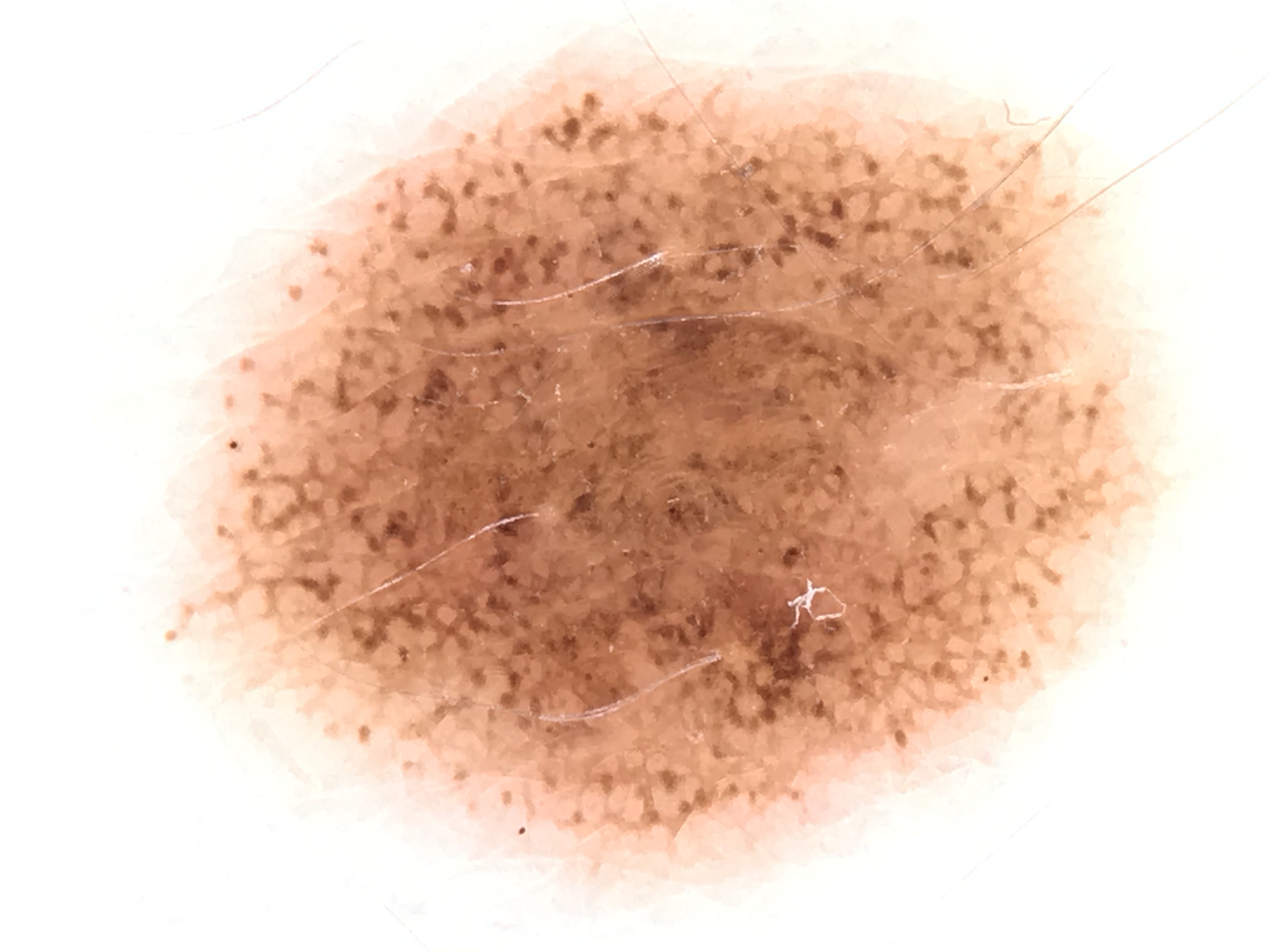| field | value |
|---|---|
| label | dysplastic junctional nevus (expert consensus) |